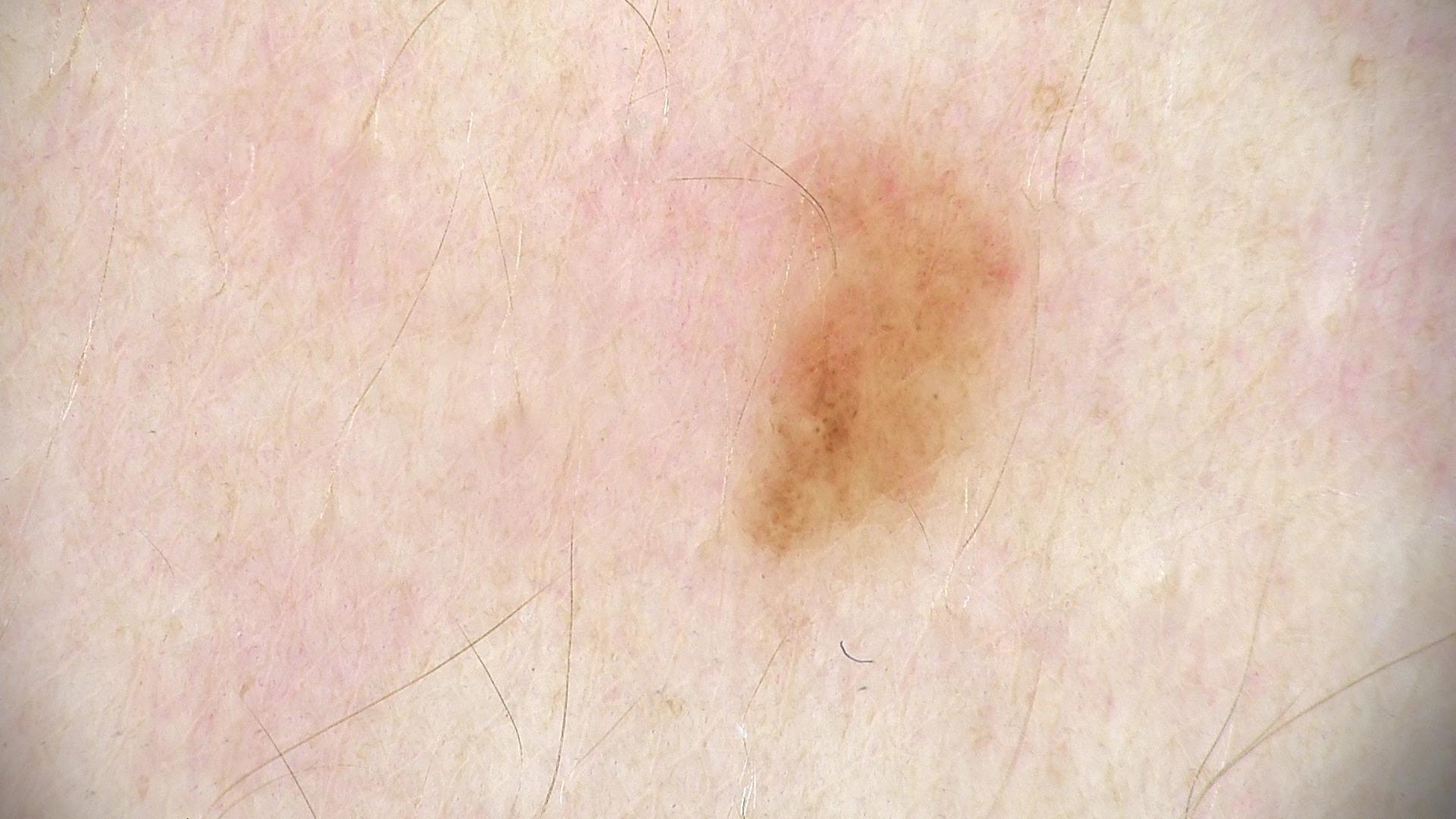Case:
– label — dysplastic junctional nevus (expert consensus)